A dermoscopic photograph of a skin lesion.
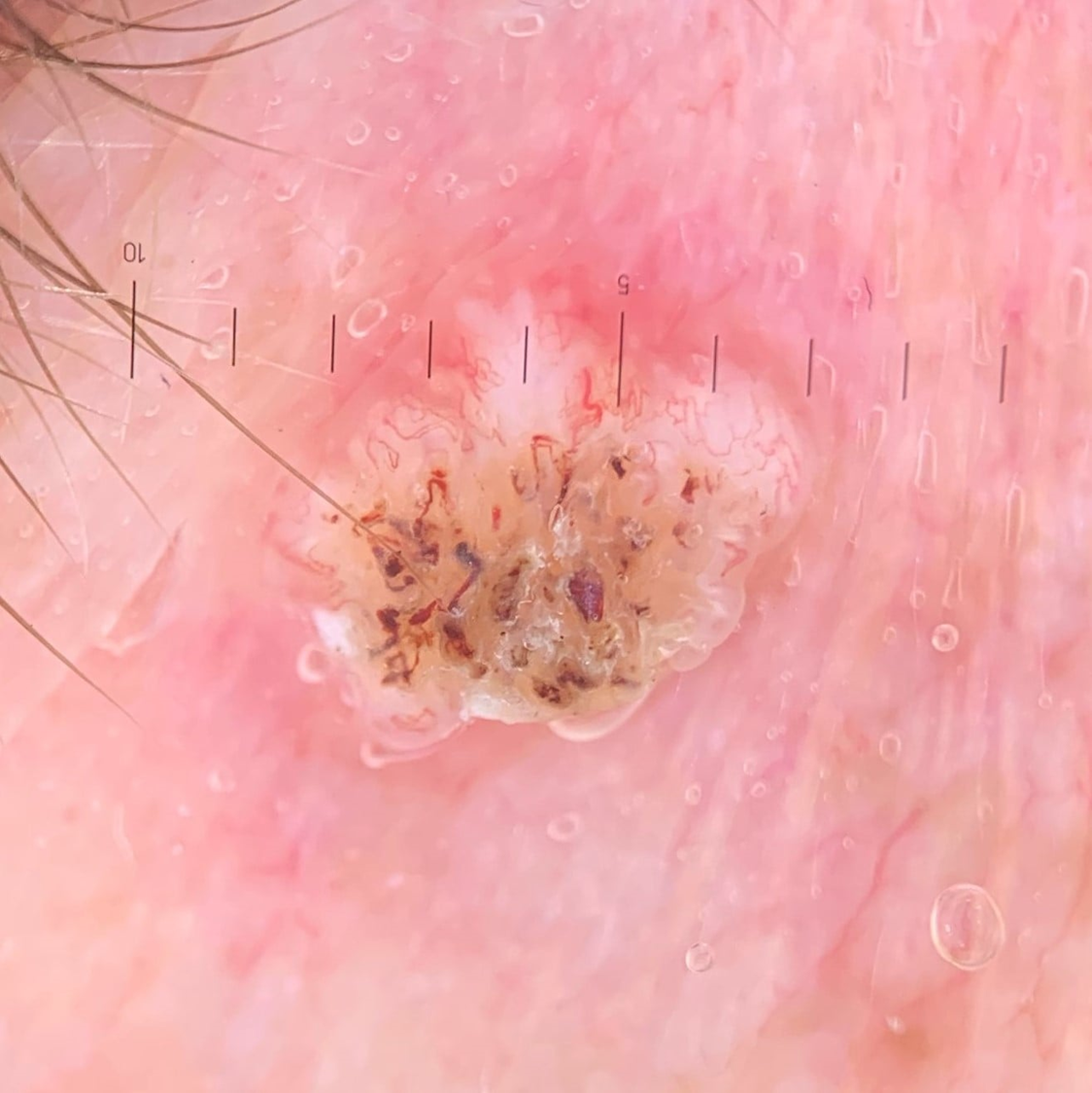The morphology is that of a keratinocytic lesion.
Histopathologically confirmed as a malignancy — a squamous cell carcinoma.